The subject is a male aged 30–39; the back of the hand is involved; the photograph is a close-up of the affected area — 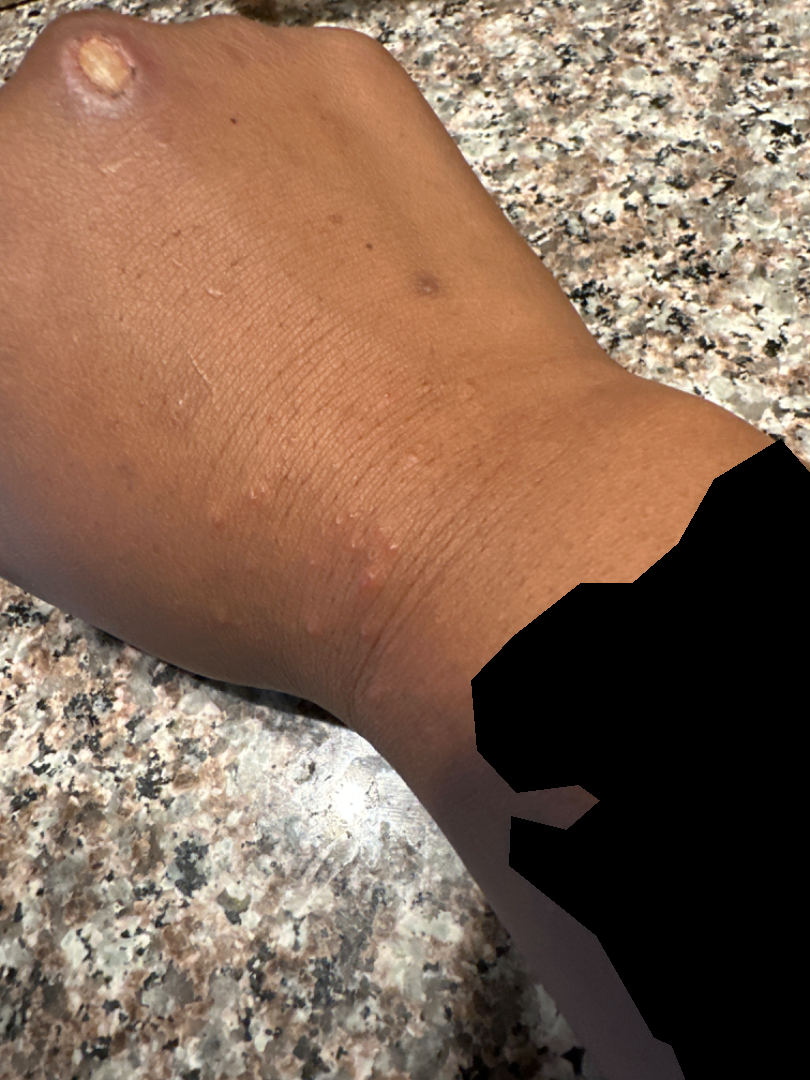<report>
<duration>about one day</duration>
<symptoms>itching, bothersome appearance</symptoms>
<patient_category>a rash</patient_category>
<skin_tone>
  <fitzpatrick>V</fitzpatrick>
  <monk_skin_tone>5</monk_skin_tone>
</skin_tone>
<differential>
  <leading>Folliculitis</leading>
</differential>
</report>